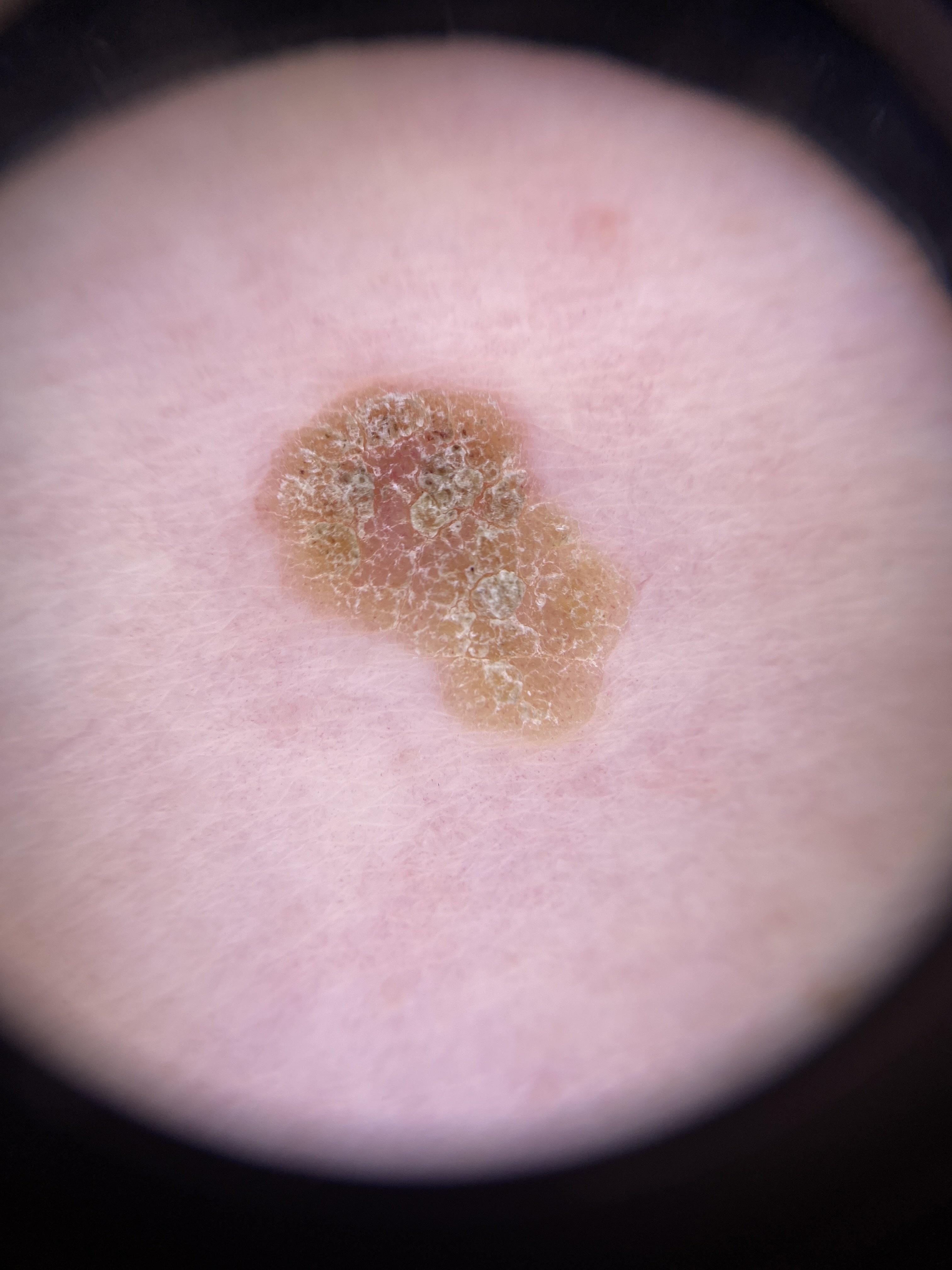| field | value |
|---|---|
| image type | dermoscopy |
| diagnostic label | Seborrheic keratosis (clinical impression) |